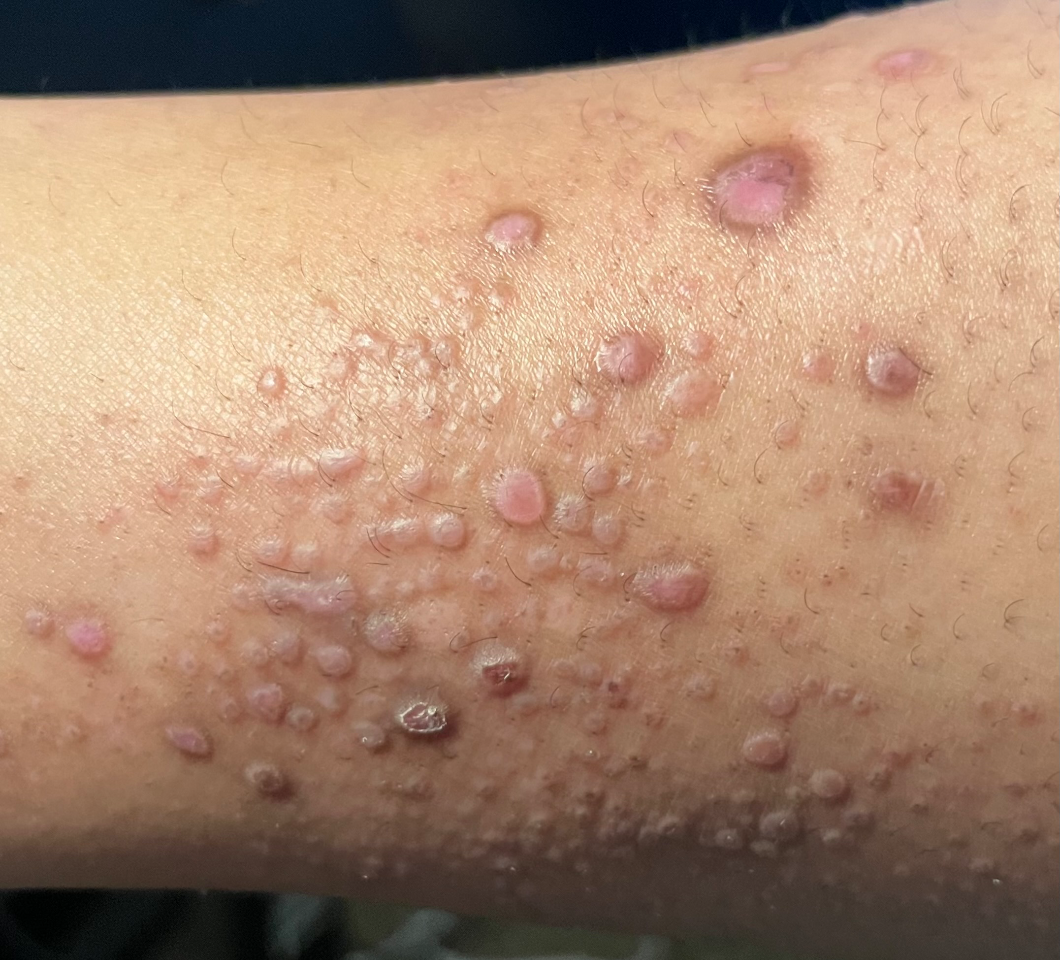The reviewing clinician's impression was: Amyloidosis of skin (weight 0.33); Pretibial myxedema (weight 0.33); Lichen Simplex Chronicus (weight 0.33).